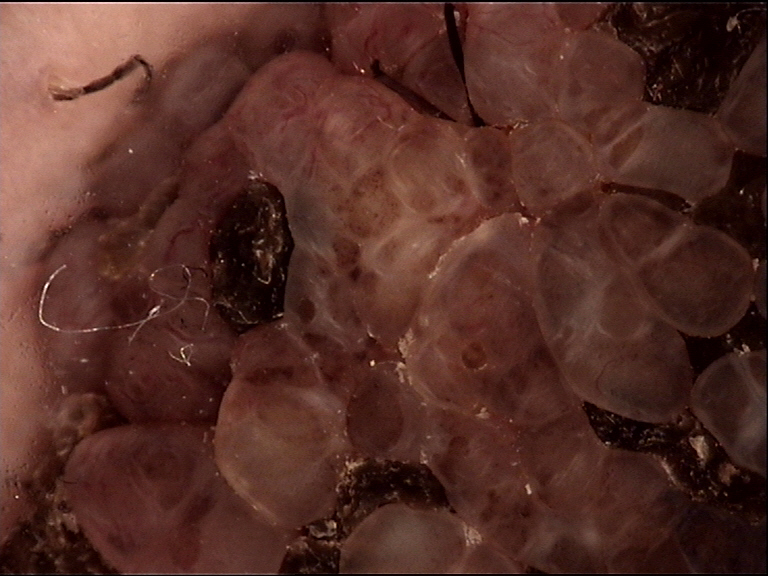The diagnosis was a banal lesion — a congenital compound nevus.